The photo was captured at an angle · the head or neck, front of the torso and arm are involved — 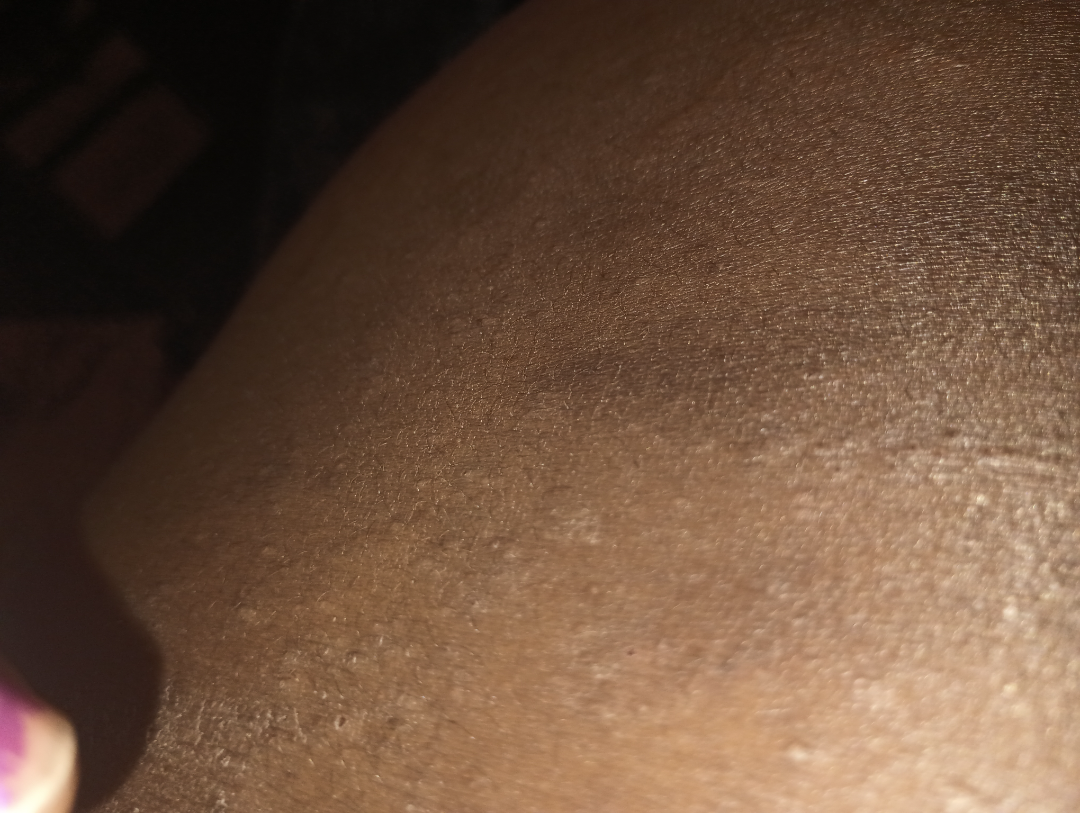| feature | finding |
|---|---|
| assessment | not assessable |
| duration | one to three months |
| patient-reported symptoms | enlargement, itching, bothersome appearance and darkening |
| patient's own categorization | a rash |